A dermoscopy image of a single skin lesion: 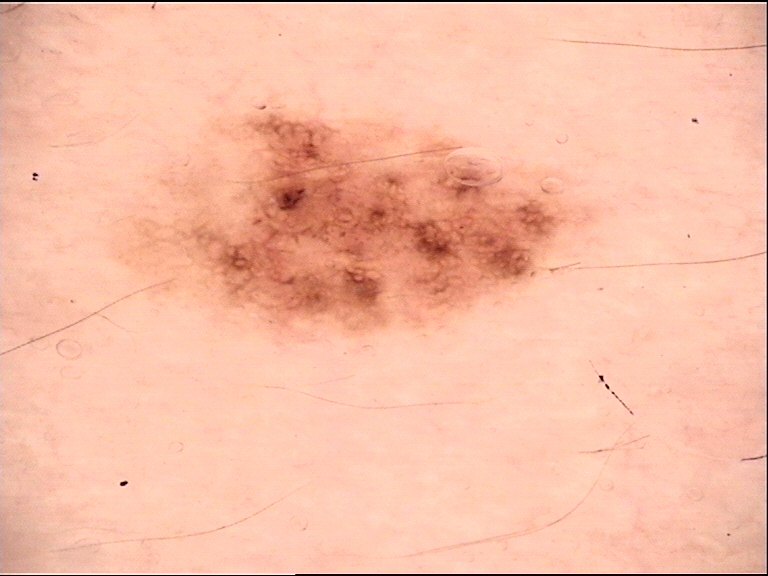| field | value |
|---|---|
| diagnostic label | dysplastic junctional nevus (expert consensus) |